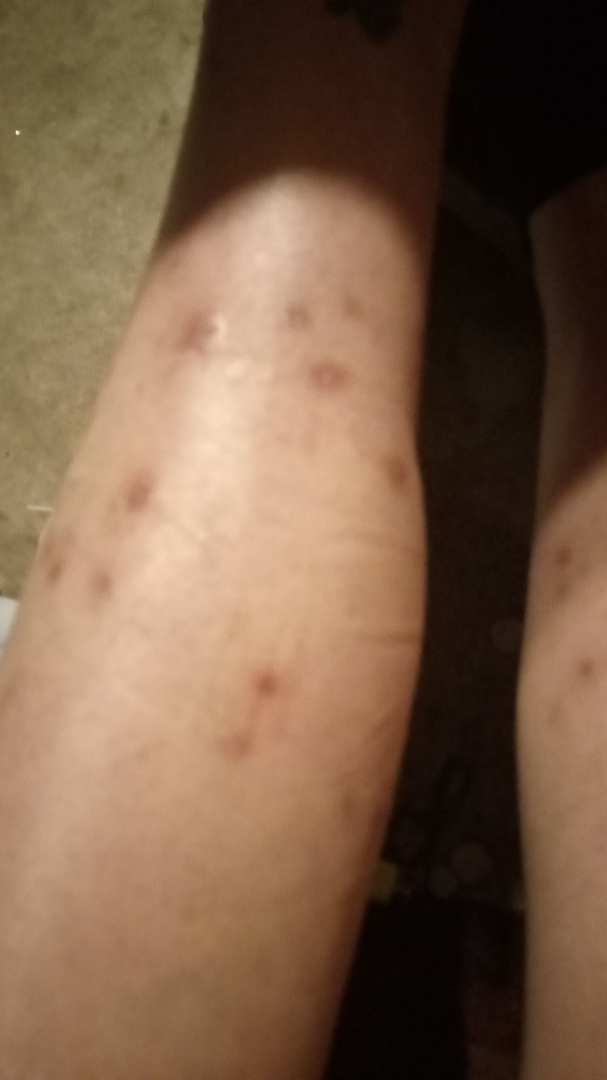assessment — not assessable | site — arm and leg | subject — female | associated systemic symptoms — none reported | image framing — close-up | symptoms — darkening and enlargement.